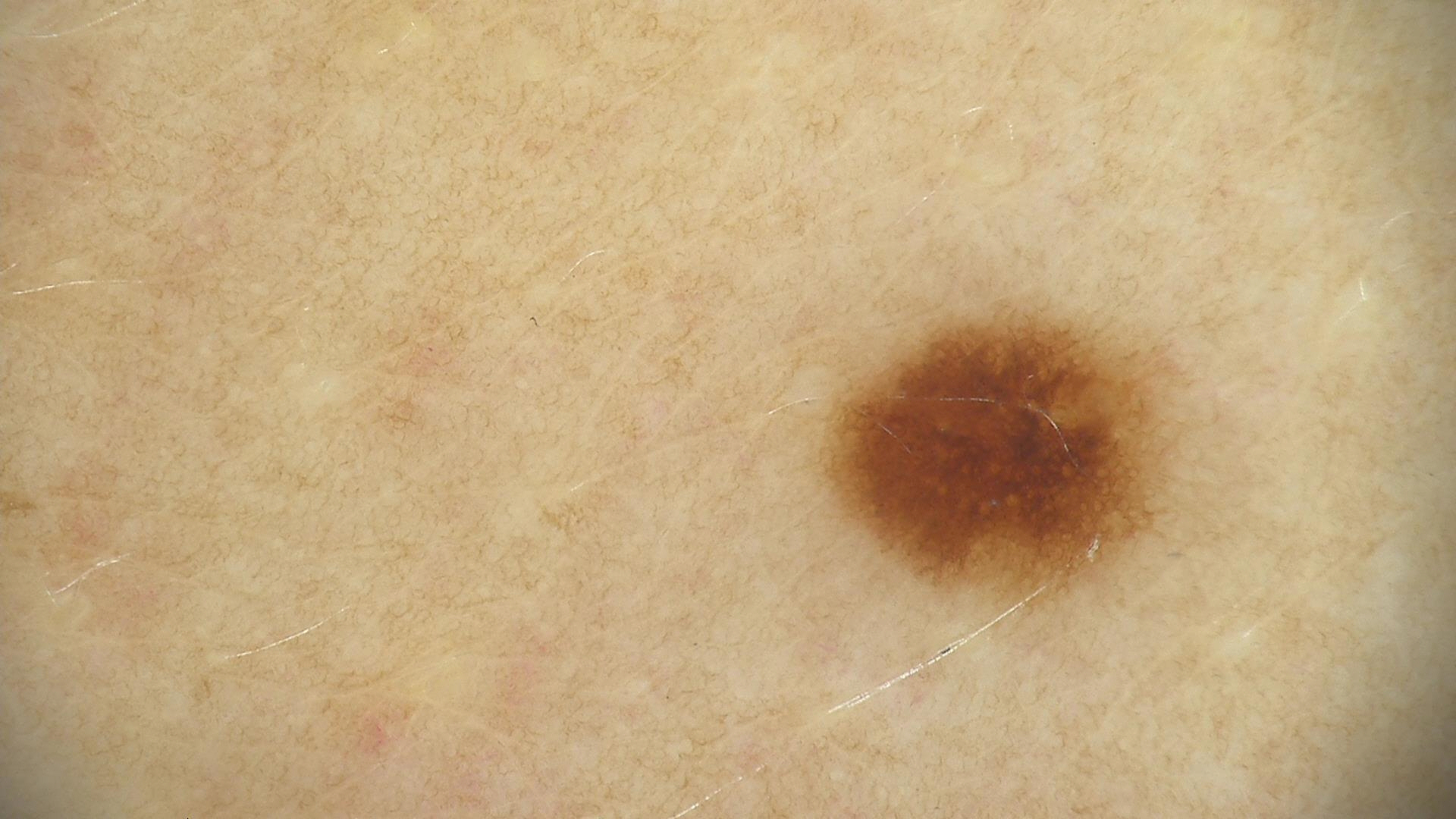{
  "diagnosis": {
    "name": "dysplastic junctional nevus",
    "code": "jd",
    "malignancy": "benign",
    "super_class": "melanocytic",
    "confirmation": "expert consensus"
  }
}